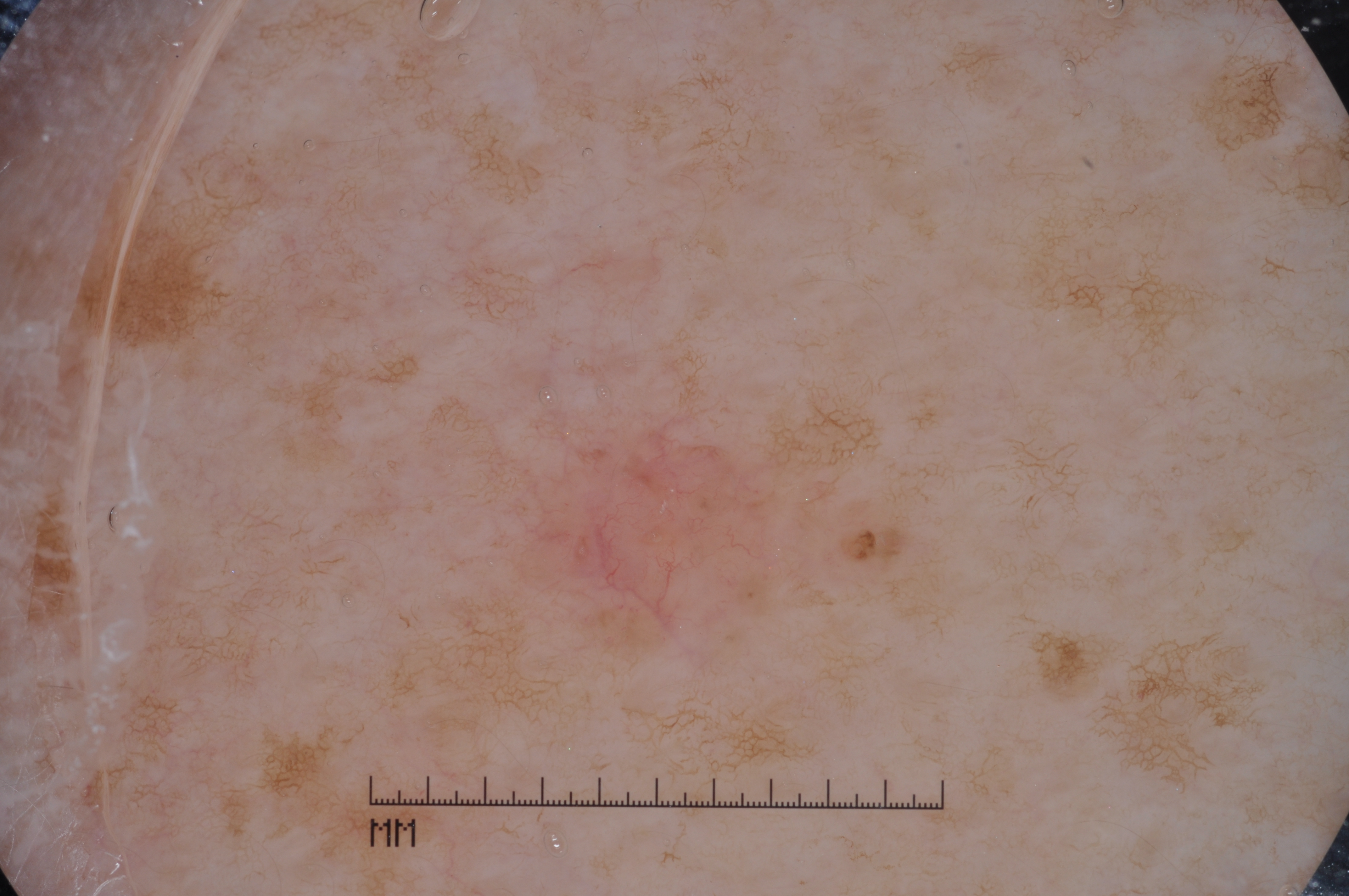The subject is a female about 50 years old. A dermoscopic image of a skin lesion. Dermoscopic review identifies pigment network and milia-like cysts, with no negative network or streaks. As (left, top, right, bottom), the lesion's extent is 514, 431, 810, 673. Consistent with a melanocytic nevus, a benign lesion.